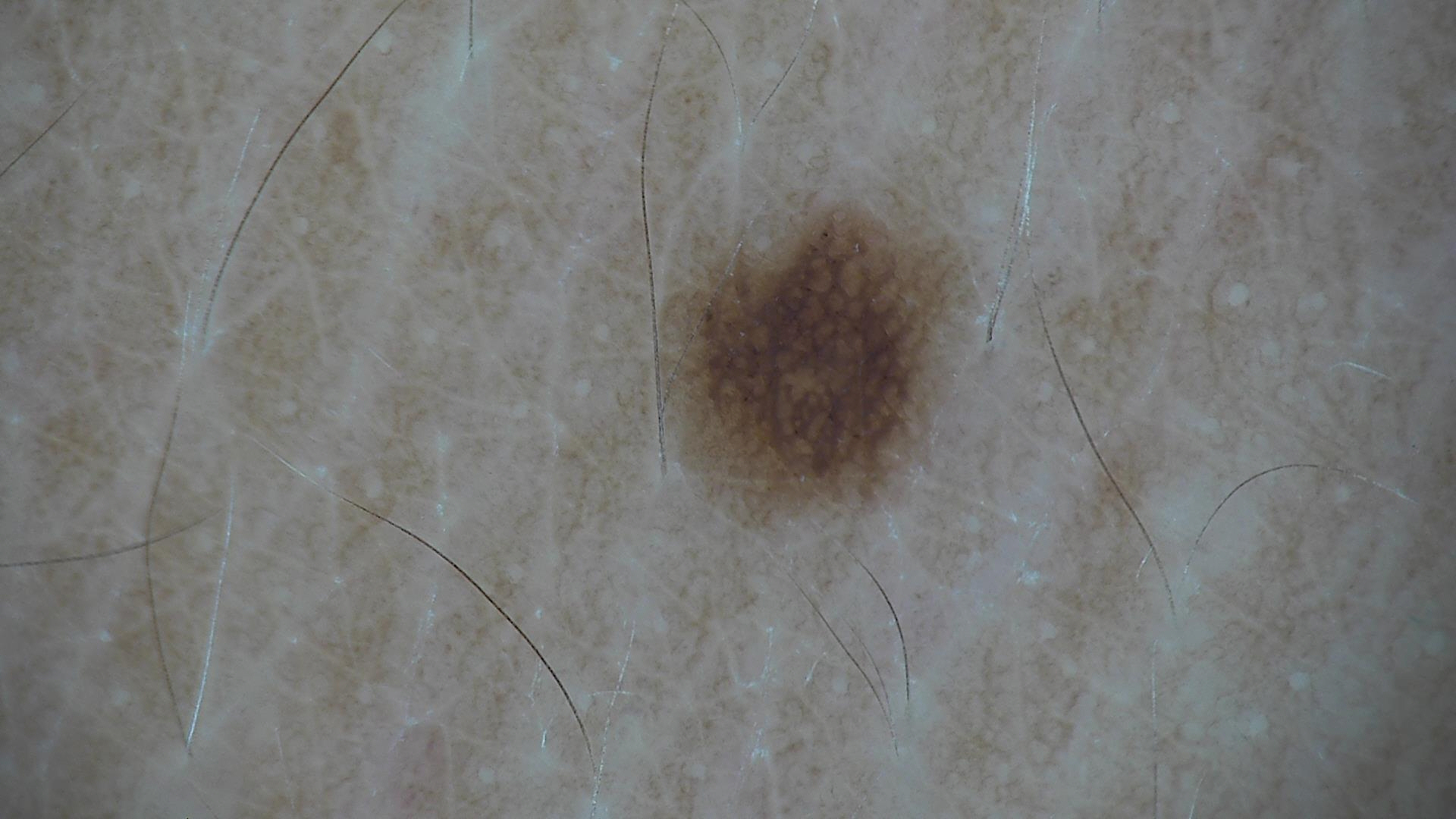{"image": "dermoscopy", "diagnosis": {"name": "dysplastic junctional nevus", "code": "jd", "malignancy": "benign", "super_class": "melanocytic", "confirmation": "expert consensus"}}